A dermoscopy image of a single skin lesion.
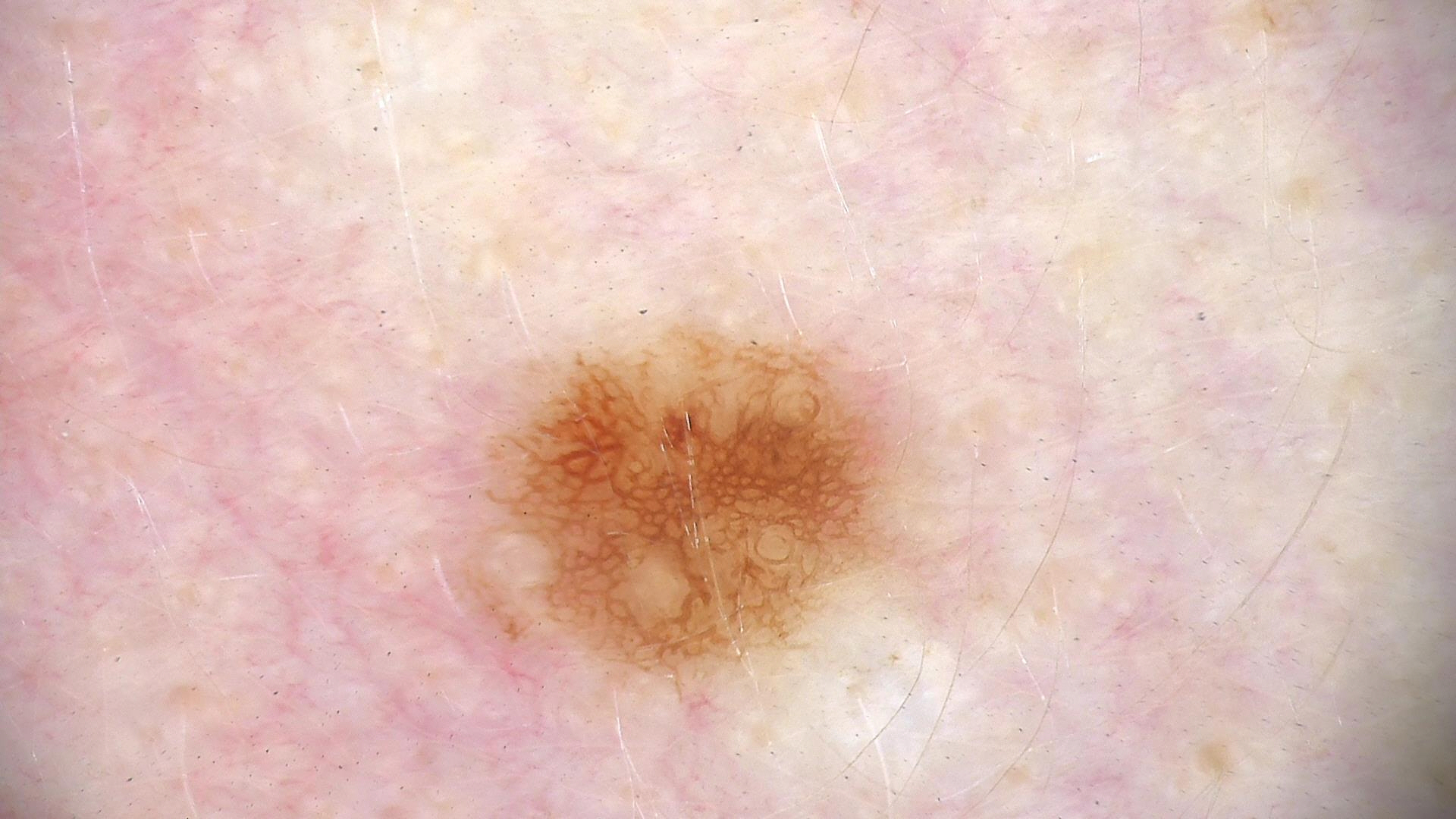label = dysplastic junctional nevus (expert consensus).